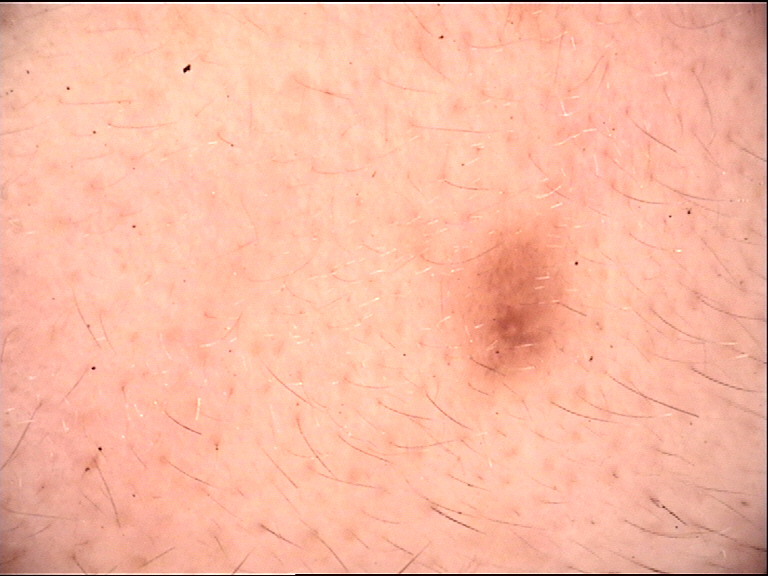A skin lesion imaged with a dermatoscope. The diagnosis was a Miescher nevus.